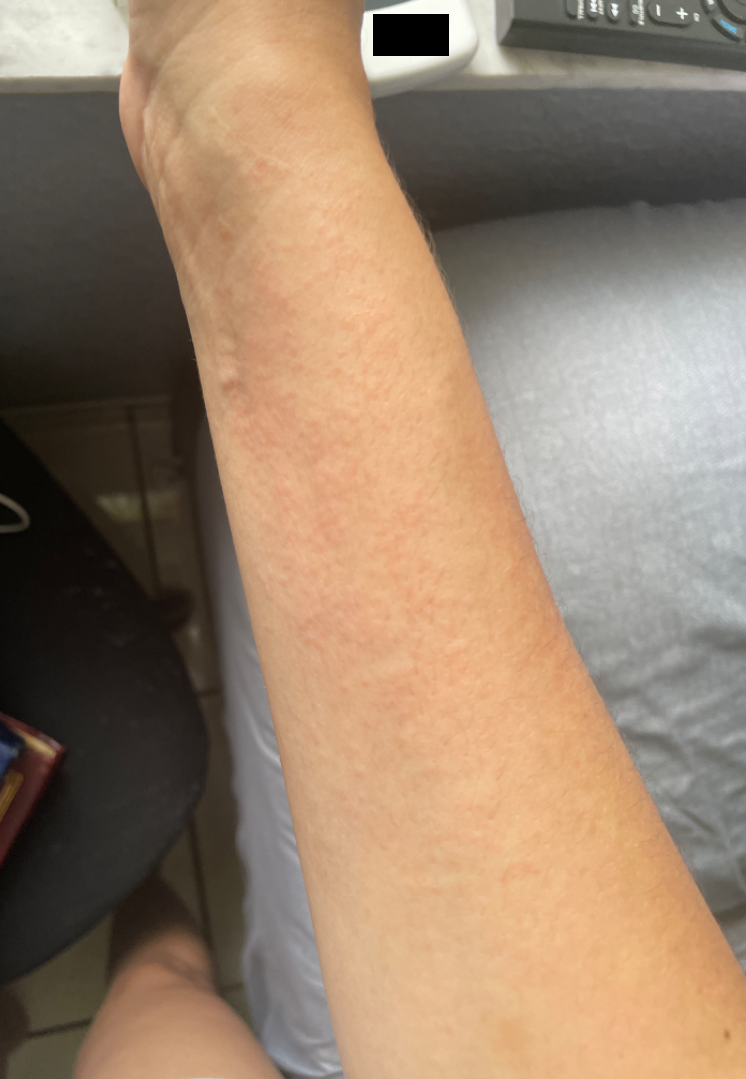Self-categorized by the patient as a rash. Female patient, age 30–39. The lesion involves the arm. The photograph was taken at a distance. The patient reports the lesion is raised or bumpy. The condition has been present for about one day. The patient reports itching. On remote dermatologist review: Eczema (1.00).